A close-up photograph: 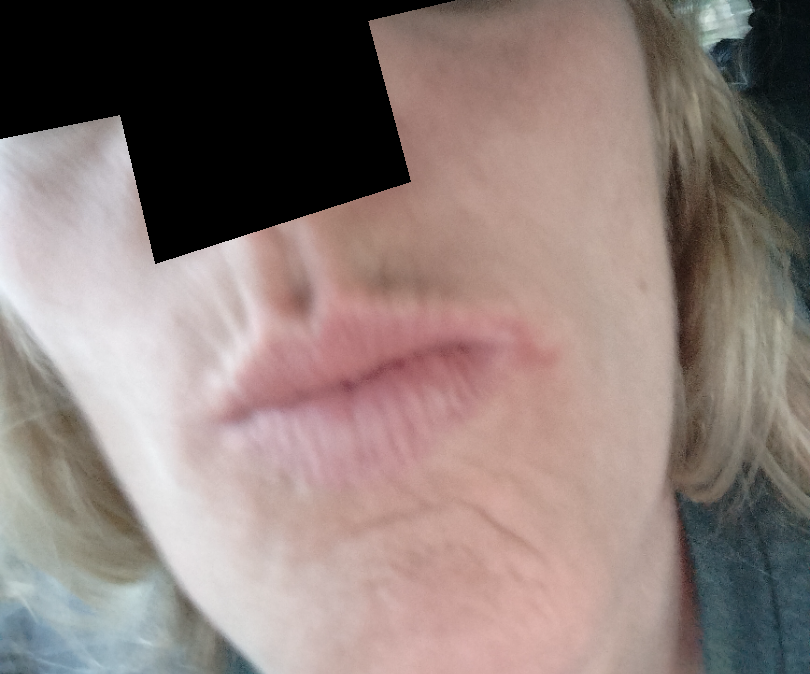Impression:
The dermatologist could not determine a likely condition from the photograph alone.